This image was taken at an angle · male subject, age 50–59 · the affected area is the back of the torso and leg:
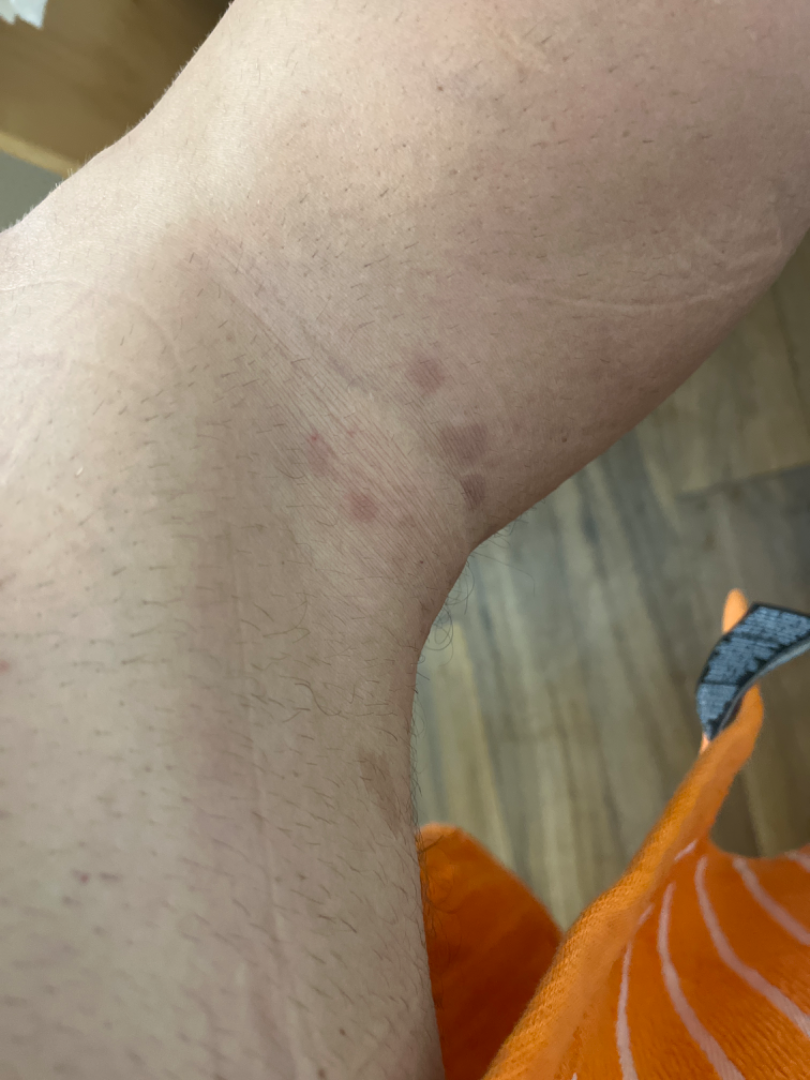Diagnostic features were not clearly distinguishable in this photograph.